The contributor is 18–29, female; the lesion involves the back of the hand; a close-up photograph:
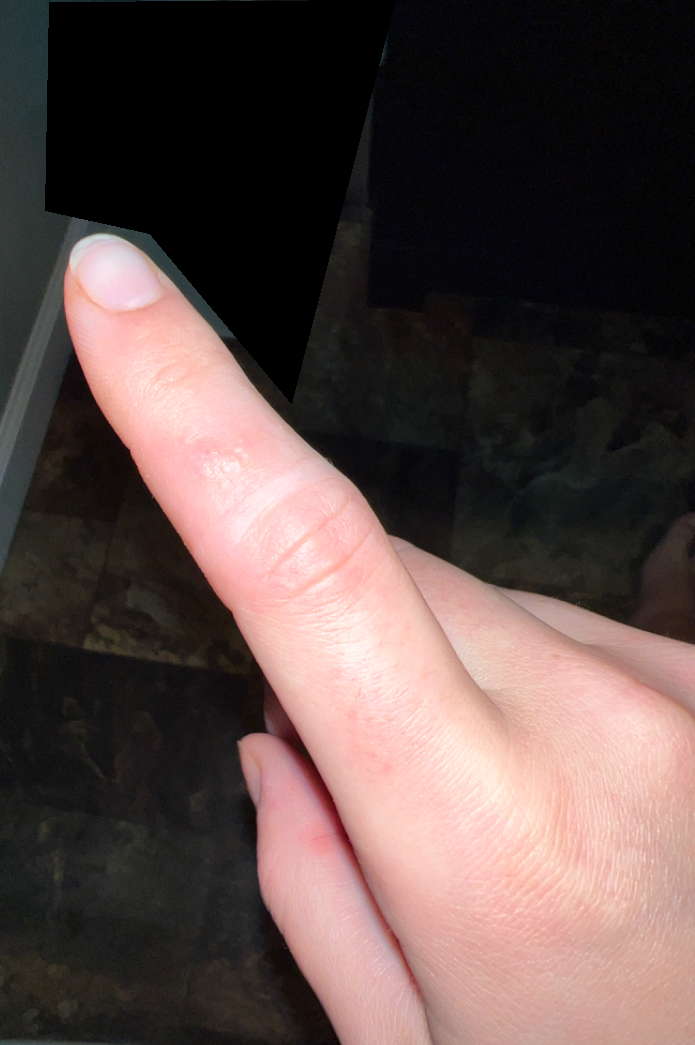The skin findings could not be characterized from the image.
The patient reports itching, enlargement and burning.
Self-categorized by the patient as a rash.
Reported duration is less than one week.
The patient reports the lesion is fluid-filled.
No constitutional symptoms were reported.